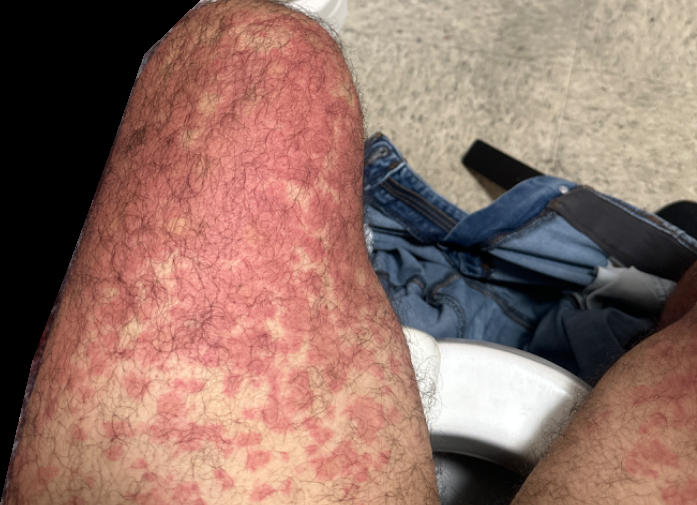patient-reported symptoms — itching and burning
skin tone — Fitzpatrick phototype III; human graders estimated Monk skin tone scale 2 (US pool) or 3 (India pool)
framing — at a distance
surface texture — flat
subject — male
location — leg
diagnostic considerations — Drug Rash and Vasculitis of the skin were each considered, in no particular order; less probable is Rocky Mountain spotted fever